A dermoscopic photograph of a skin lesion: 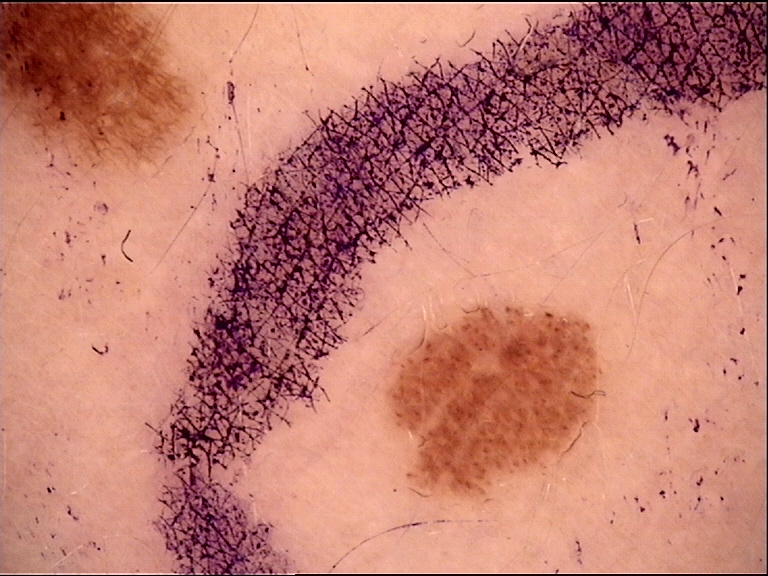Classified as a dysplastic junctional nevus.